The lesion is described as raised or bumpy · the condition has been present for less than one week · skin tone: FST IV; lay graders estimated 5 on the MST · self-categorized by the patient as a rash · the subject is 18–29, male · reported lesion symptoms include itching · close-up view · no constitutional symptoms were reported · located on the back of the hand, palm and arm: 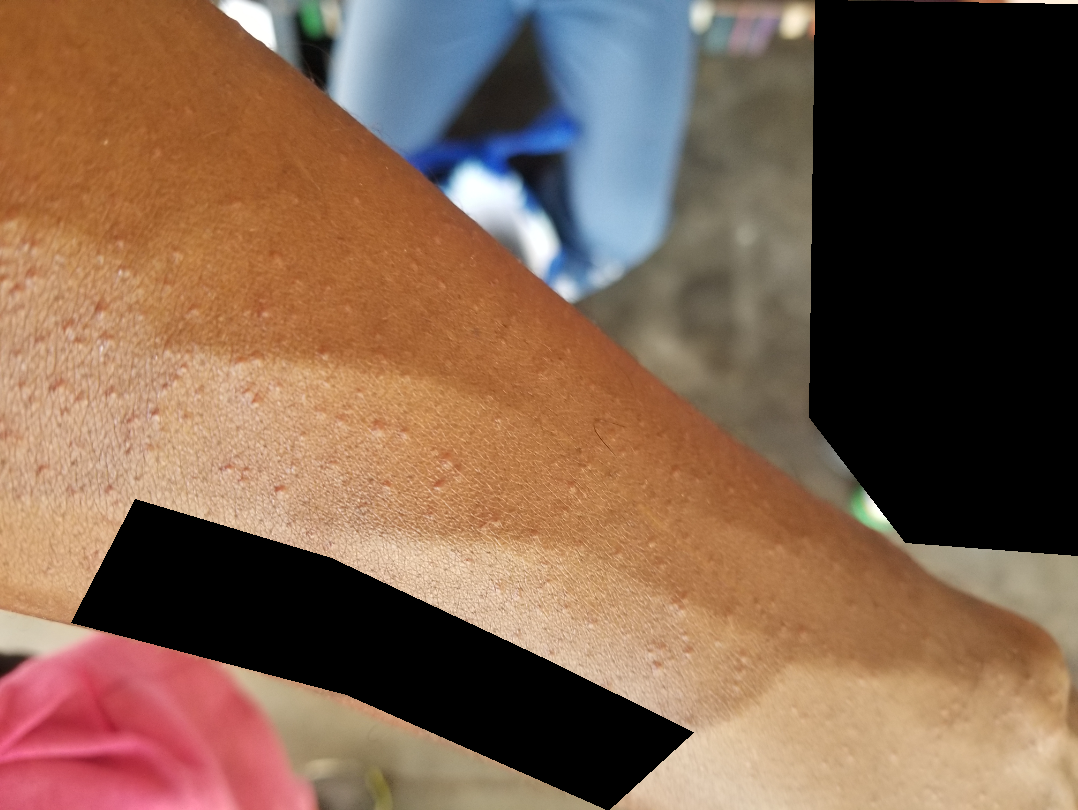One reviewing dermatologist: most consistent with Lichen nitidus; an alternative is Eczema; also raised was Hypersensitivity.